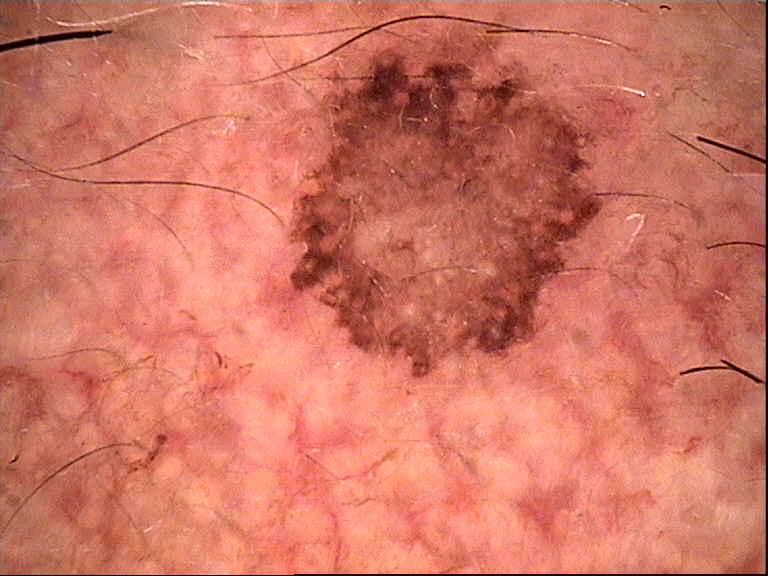Summary:
This is a keratinocytic lesion.
Conclusion:
Classified as a seborrheic keratosis.